Imaged for a research study, with no referral diagnosis recorded · a clinical close-up of a skin lesion · the patient says their skin reddens painfully with sun exposure.
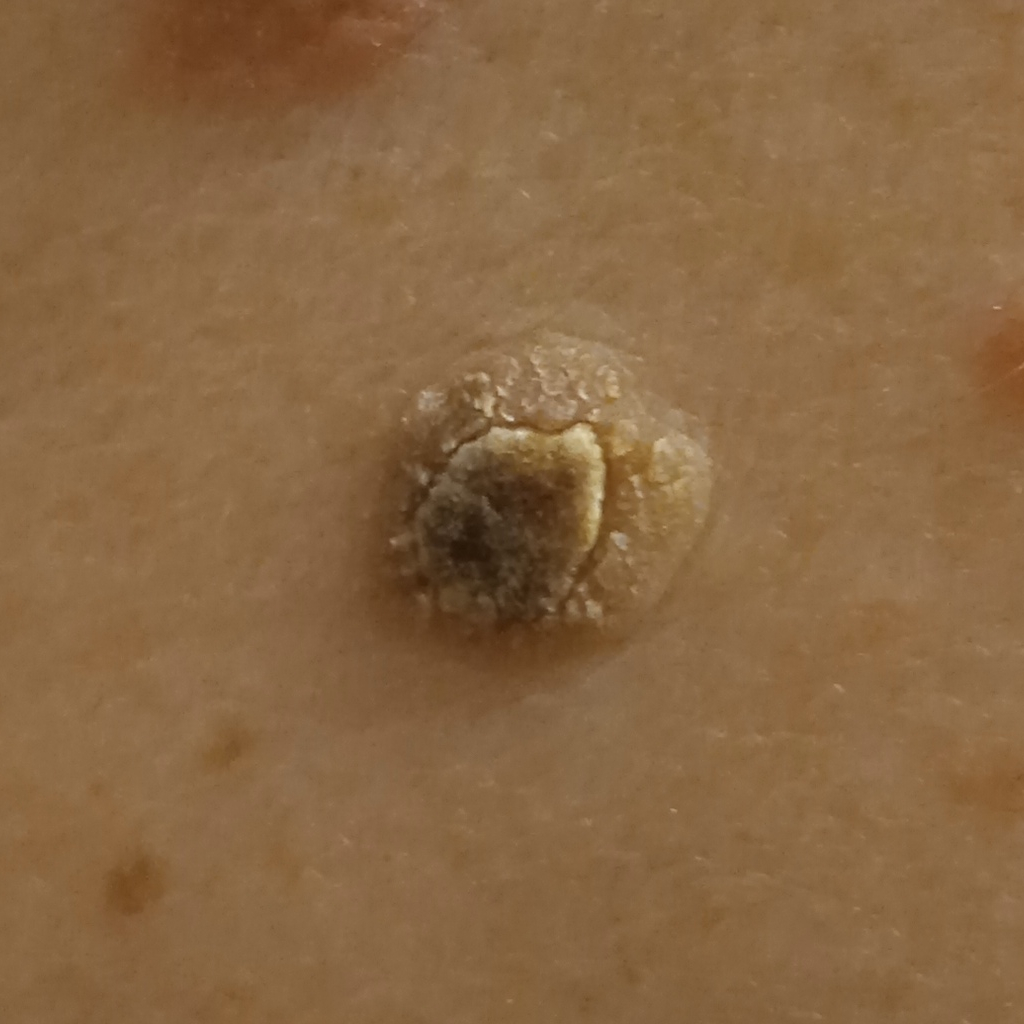Summary:
Located on the back.
Conclusion:
The lesion was assessed as a seborrheic keratosis.